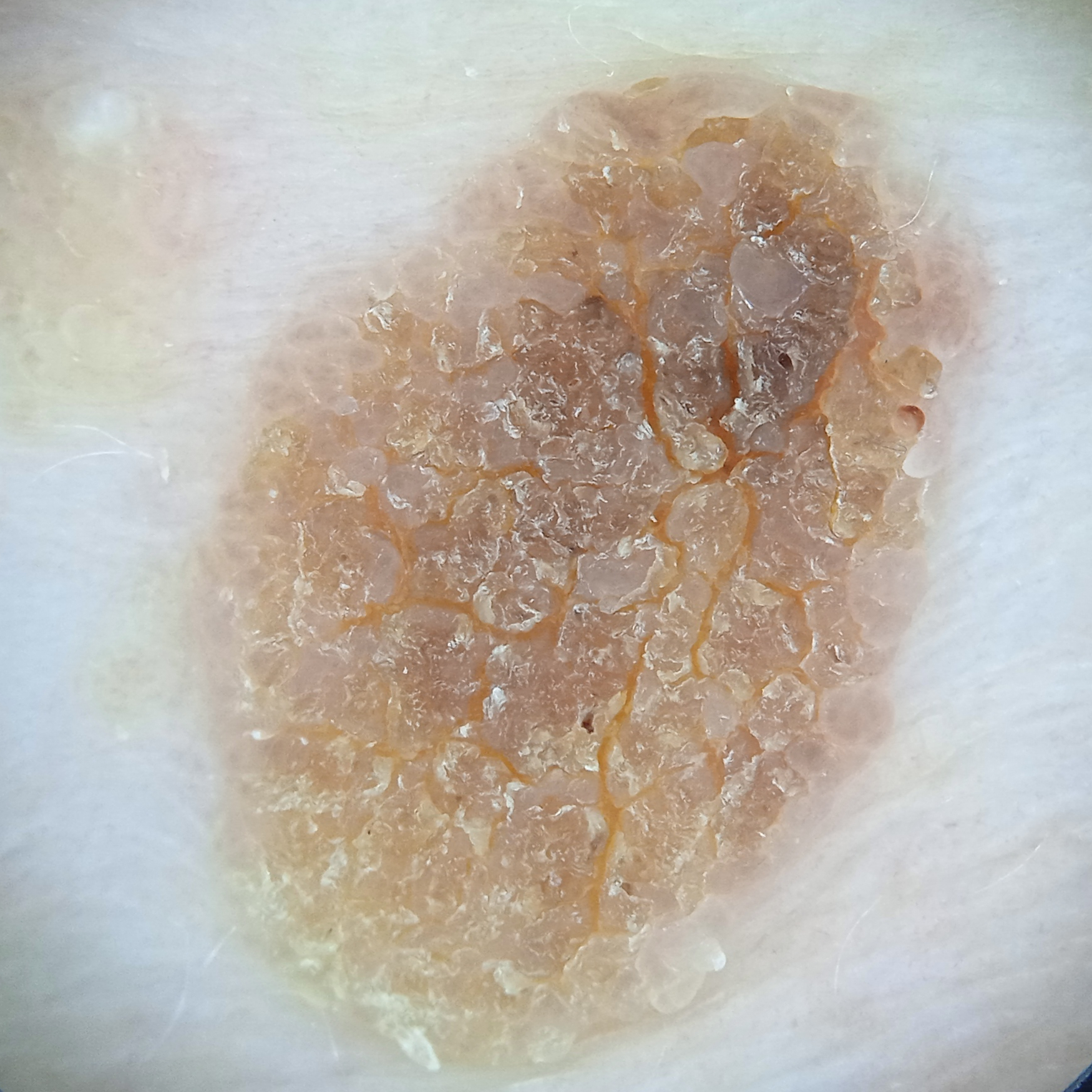image: dermoscopic image
subject: female, 81 years old
referral context: research study (no referral diagnosis)
nevus count: a moderate number of melanocytic nevi
site: the torso
size: 12.2 mm
assessment: seborrheic keratosis (dermatologist consensus)